A skin lesion imaged with a dermatoscope: 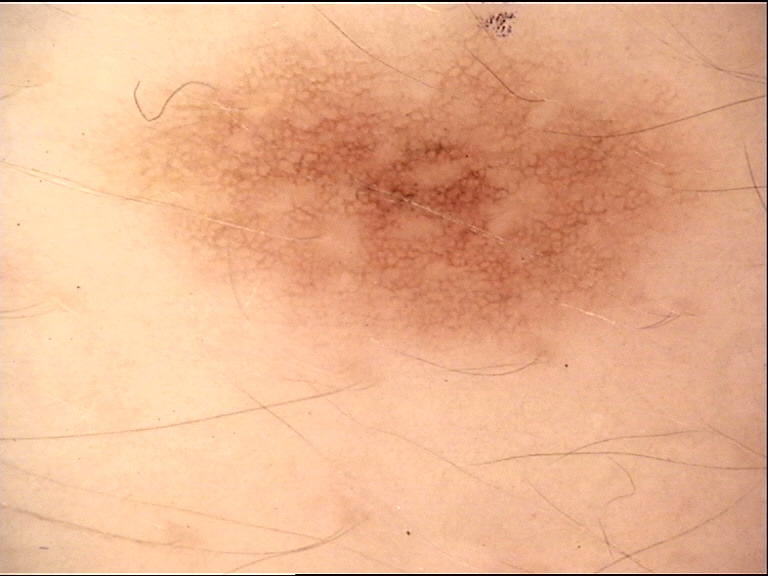The diagnostic label was a benign lesion — a dysplastic junctional nevus.